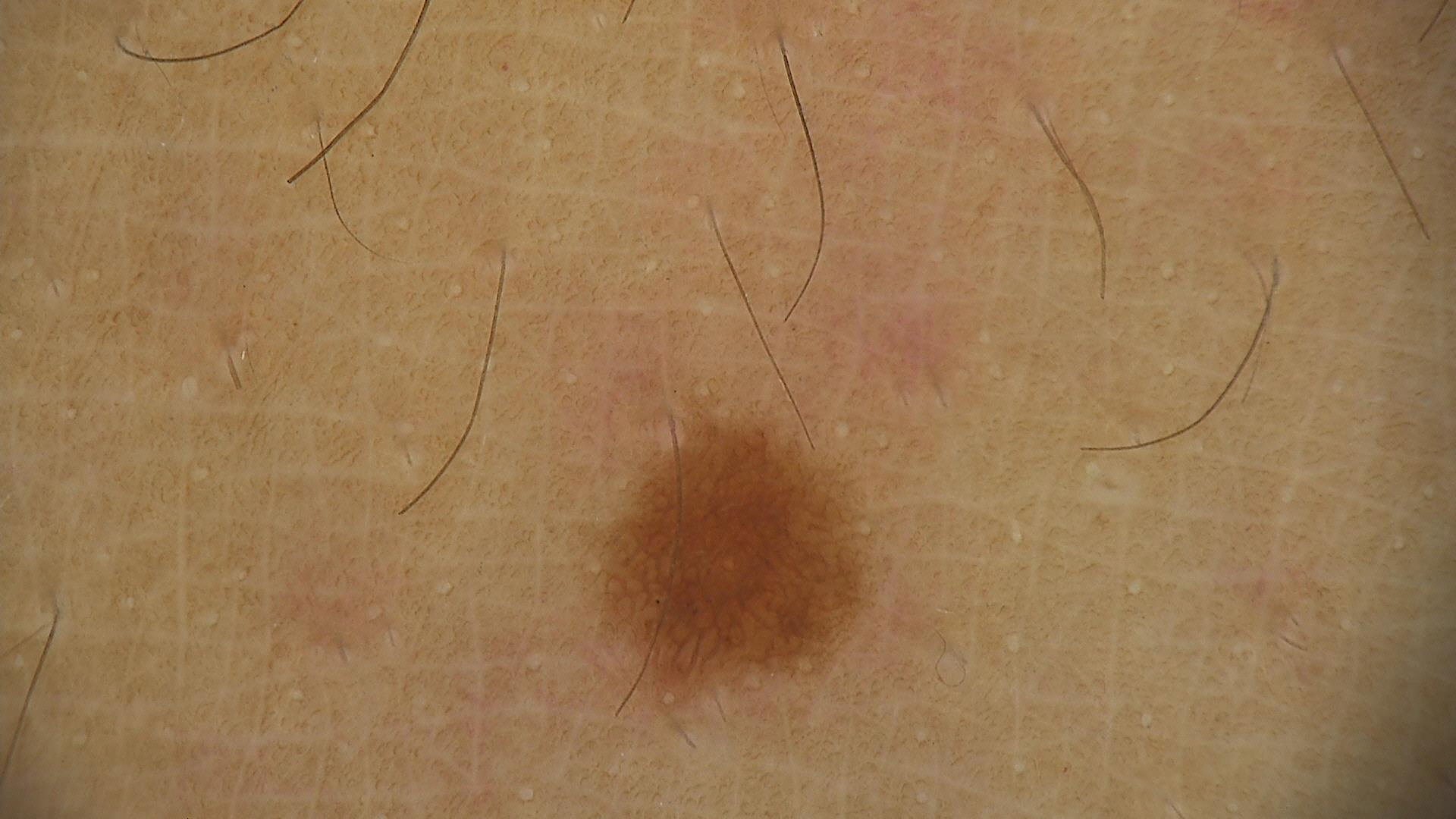Conclusion: Consistent with a junctional nevus.